The subject is male. This image was taken at an angle. The head or neck is involved:
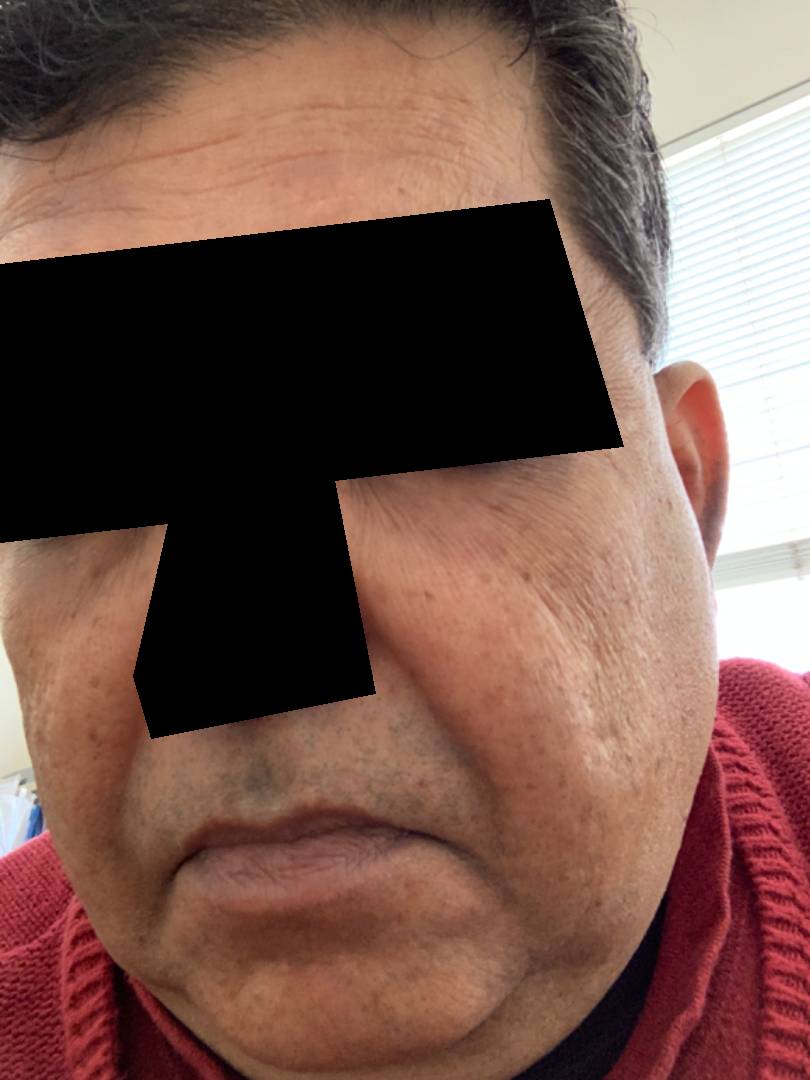assessment: ungradable on photographic review